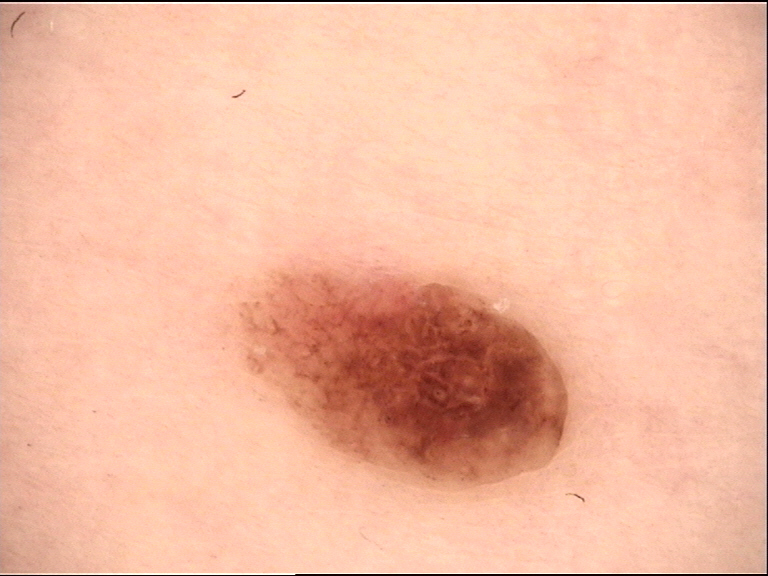| feature | finding |
|---|---|
| lesion type | banal |
| label | compound nevus (expert consensus) |